A skin lesion imaged with a dermatoscope; a female subject, approximately 50 years of age: 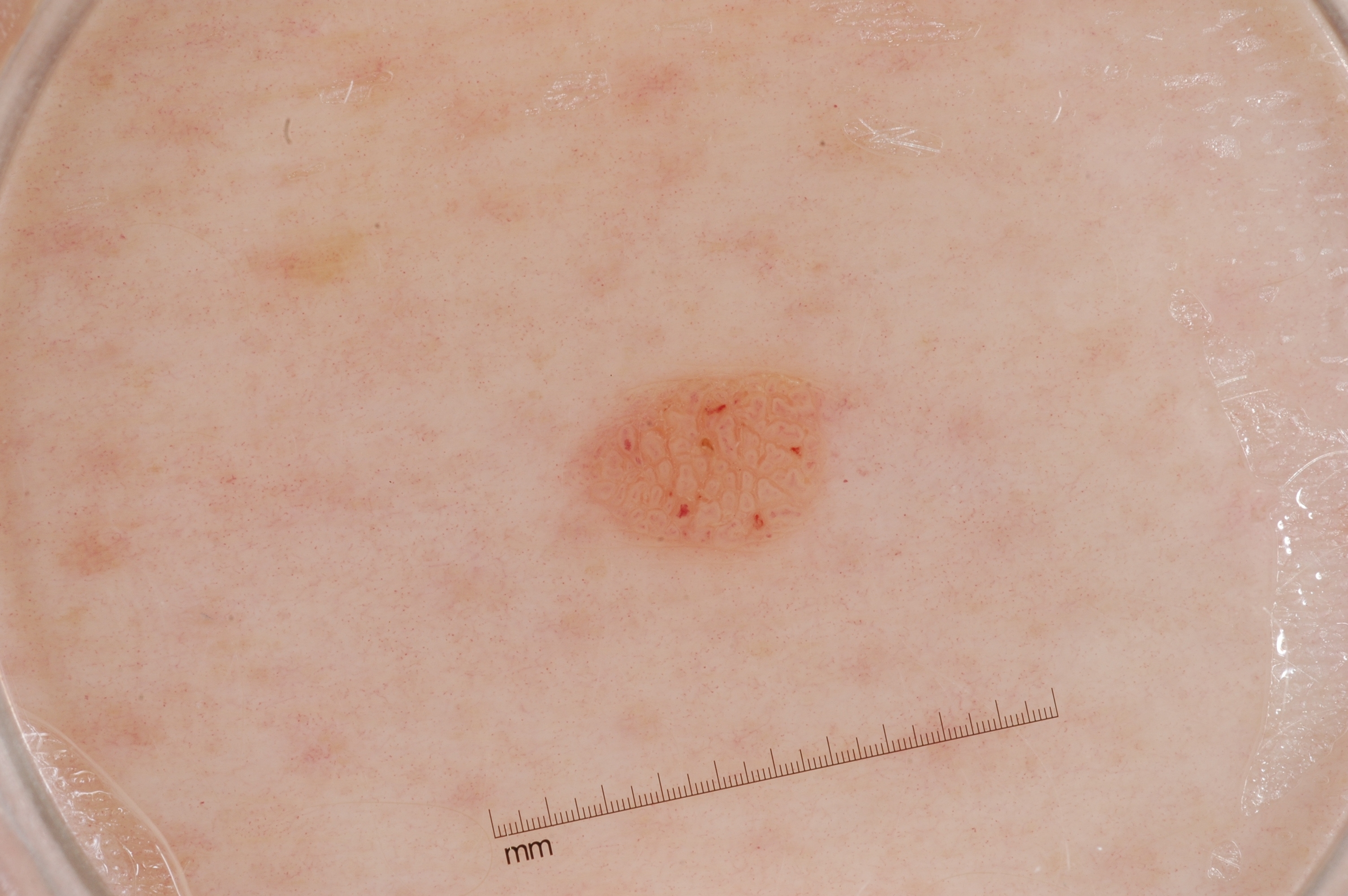<record>
<dermoscopic_features>
  <present>milia-like cysts</present>
  <absent>streaks, negative network, pigment network</absent>
</dermoscopic_features>
<lesion_location>
  <bbox_xyxy>558, 357, 853, 567</bbox_xyxy>
</lesion_location>
<diagnosis>
  <name>seborrheic keratosis</name>
  <malignancy>benign</malignancy>
  <lineage>keratinocytic</lineage>
  <provenance>clinical</provenance>
</diagnosis>
</record>